A dermoscopic image of a skin lesion.
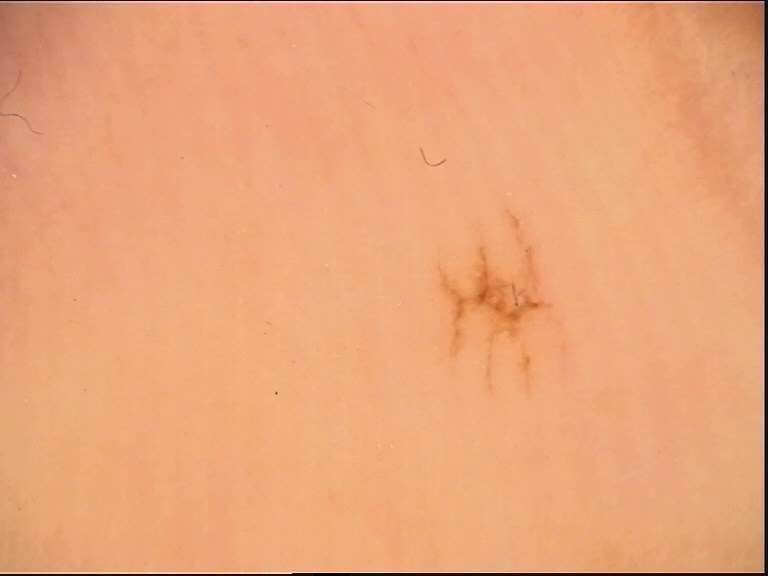label = acral junctional nevus (expert consensus).